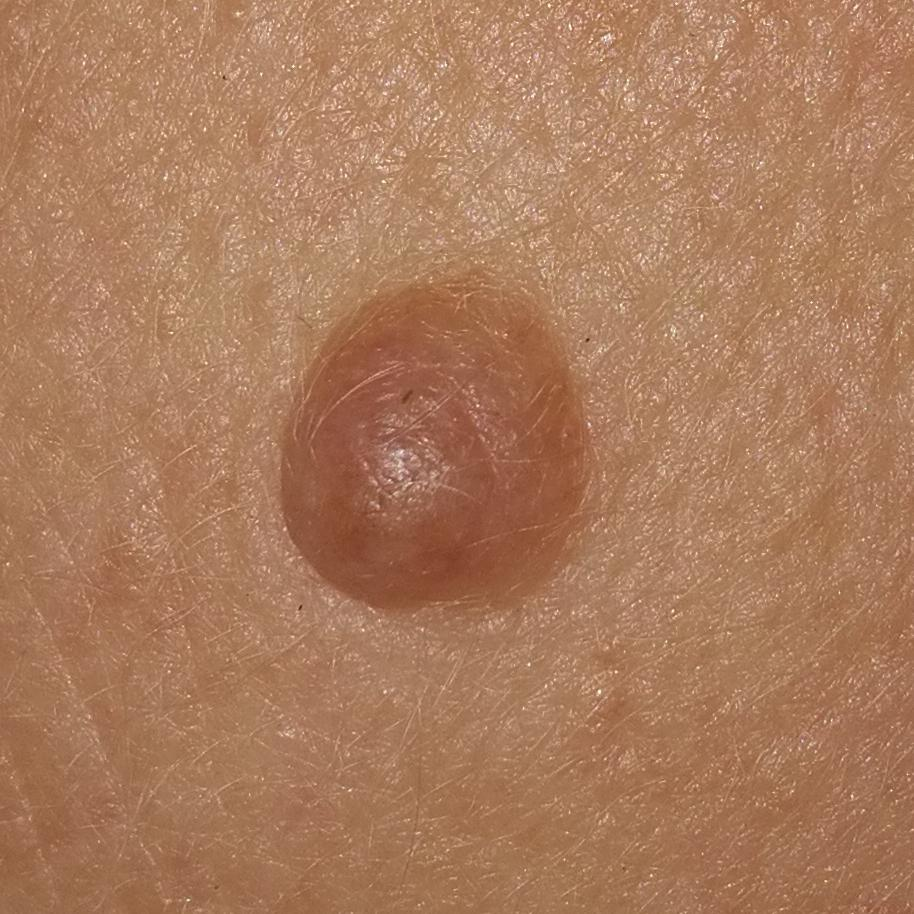A patient age 35. The lesion was found on the face. The patient describes that the lesion has grown, itches, and is elevated, but does not hurt. Consistent with a nevus.